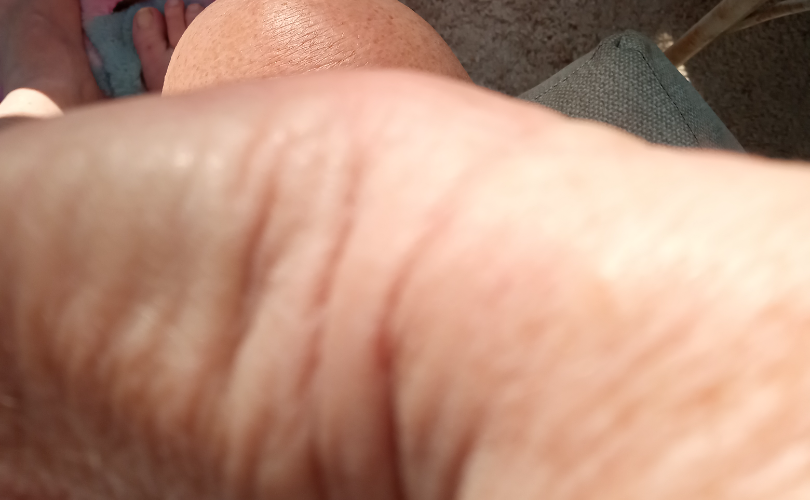– assessment · ungradable on photographic review
– site · back of the hand and arm
– shot type · close-up